The head or neck is involved · close-up view: 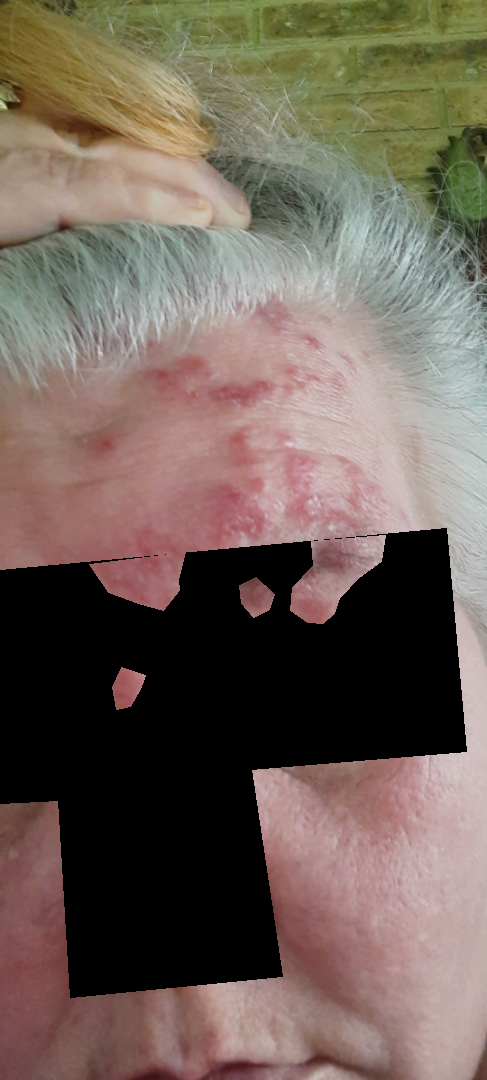The contributor notes burning, itching, bothersome appearance, pain and enlargement. The reviewing dermatologist's impression was: consistent with Herpes Zoster.